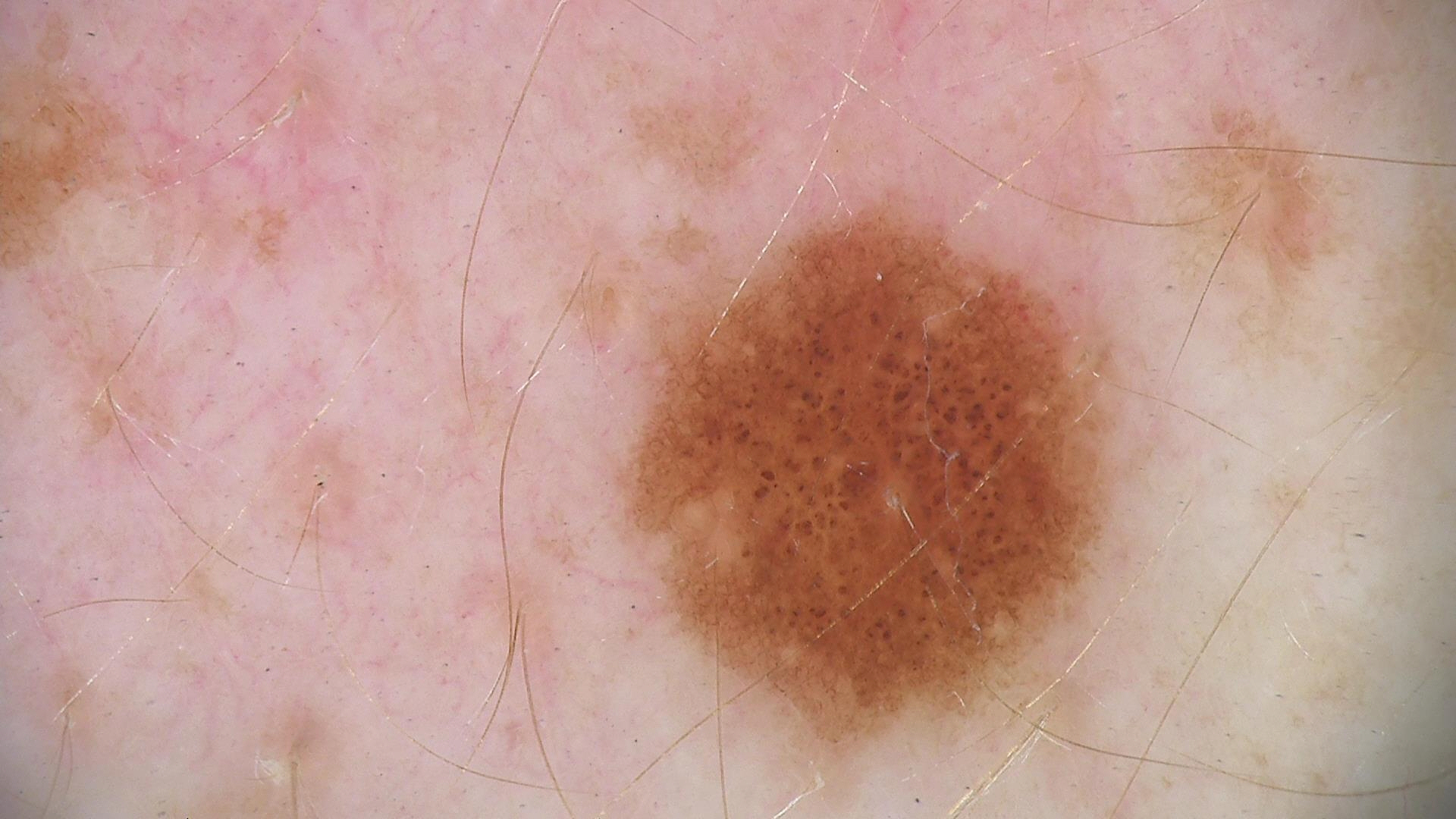A dermatoscopic image of a skin lesion. The diagnosis was a dysplastic junctional nevus.